This is a close-up image.
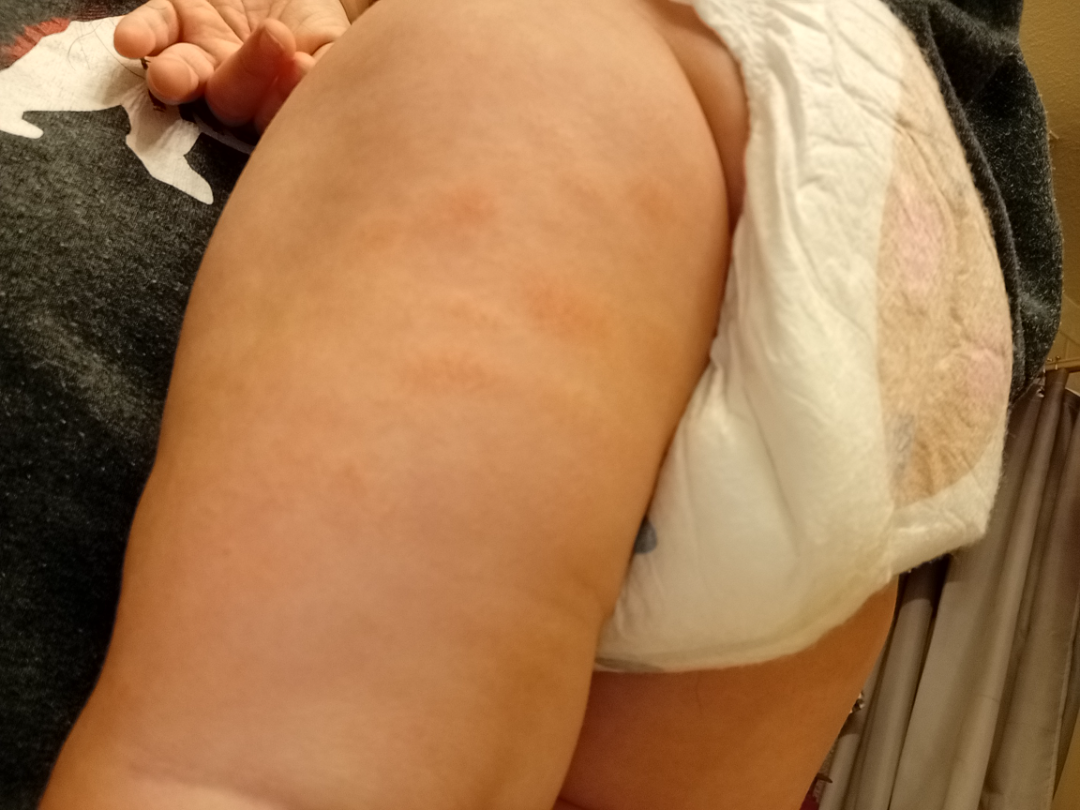Skin tone: Fitzpatrick III. Most likely Eczema; also raised was Urticaria.